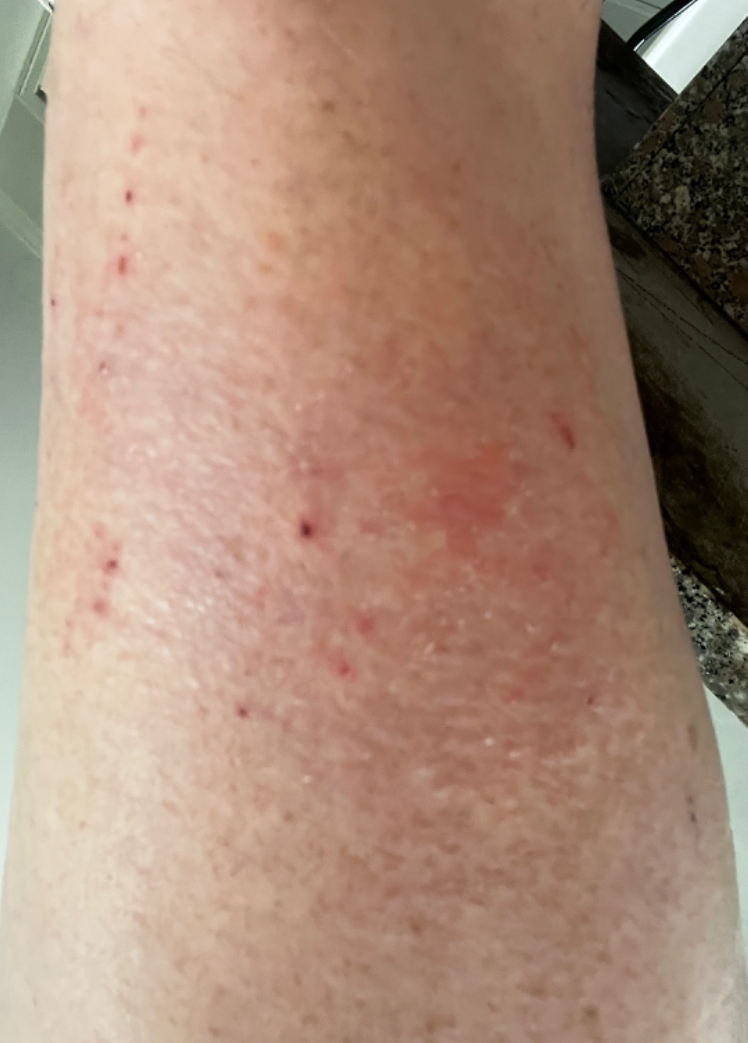The subject is a female aged 50–59. The patient indicates the condition has been present for three to twelve months. Self-categorized by the patient as a rash. The affected area is the leg. The lesion is described as rough or flaky. This is a close-up image. Skin tone: Fitzpatrick phototype III. Symptoms reported: bothersome appearance and itching. On photographic review by a dermatologist: most consistent with Acute and chronic dermatitis.